A dermoscopic close-up of a skin lesion.
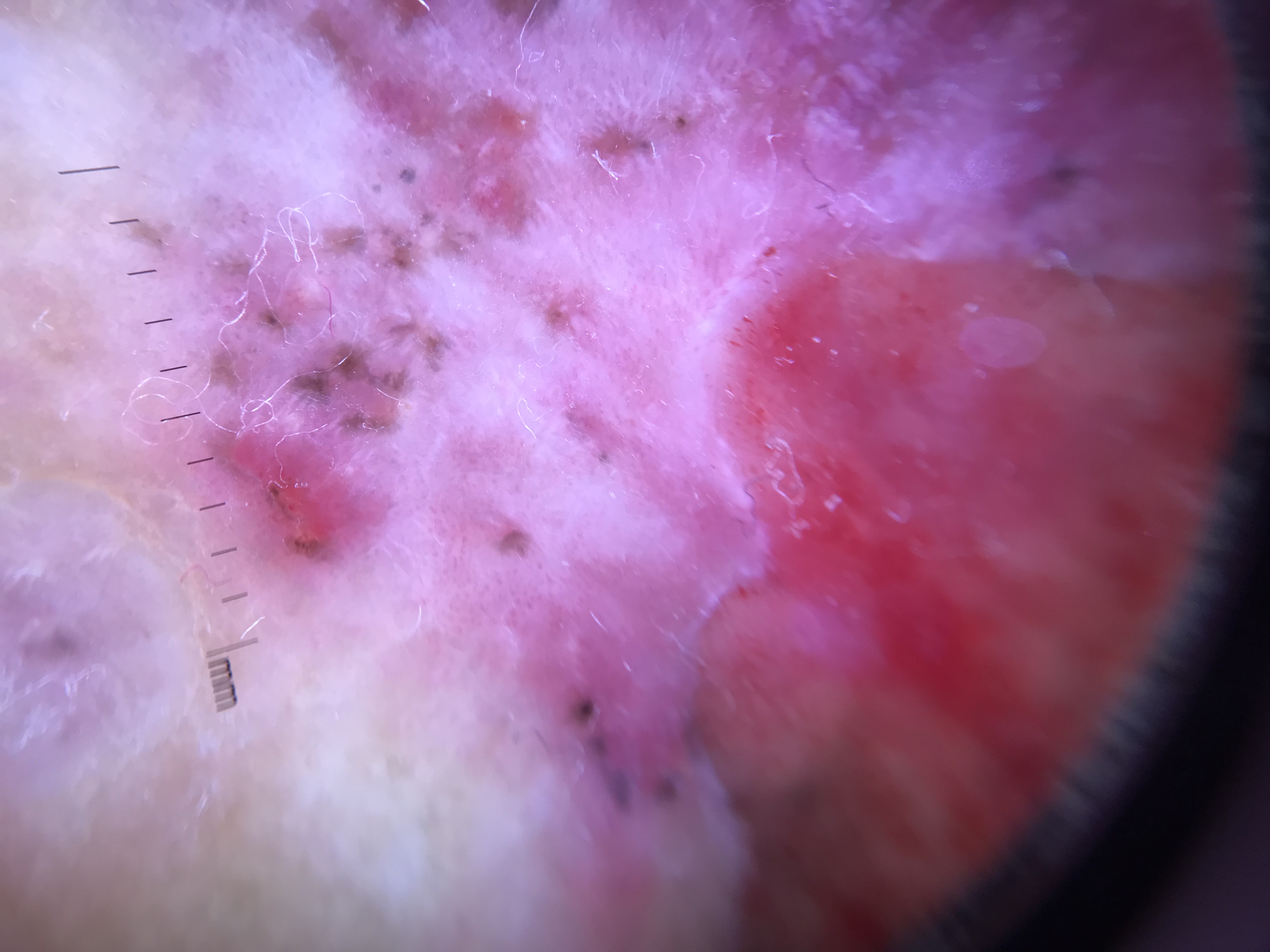{"diagnosis": {"name": "basal cell carcinoma", "code": "bcc", "malignancy": "malignant", "super_class": "non-melanocytic", "confirmation": "histopathology"}}